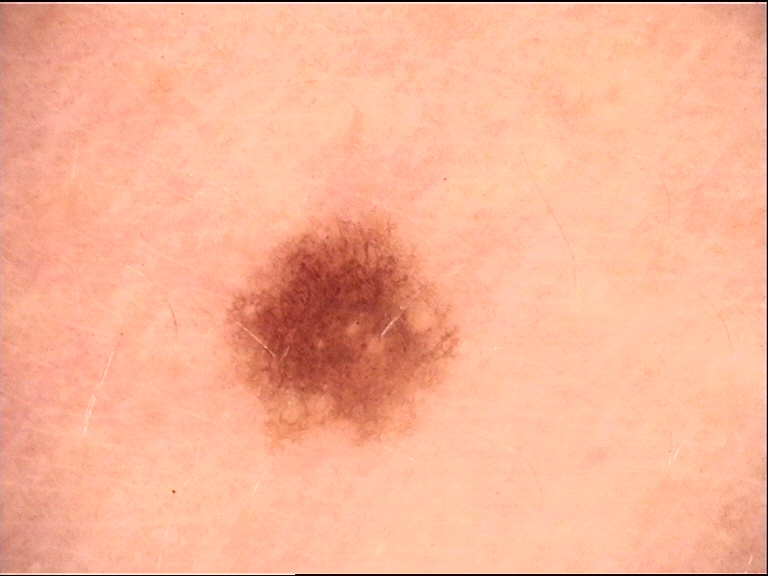A skin lesion imaged with a dermatoscope. The architecture is that of a banal lesion. The diagnostic label was a junctional nevus.